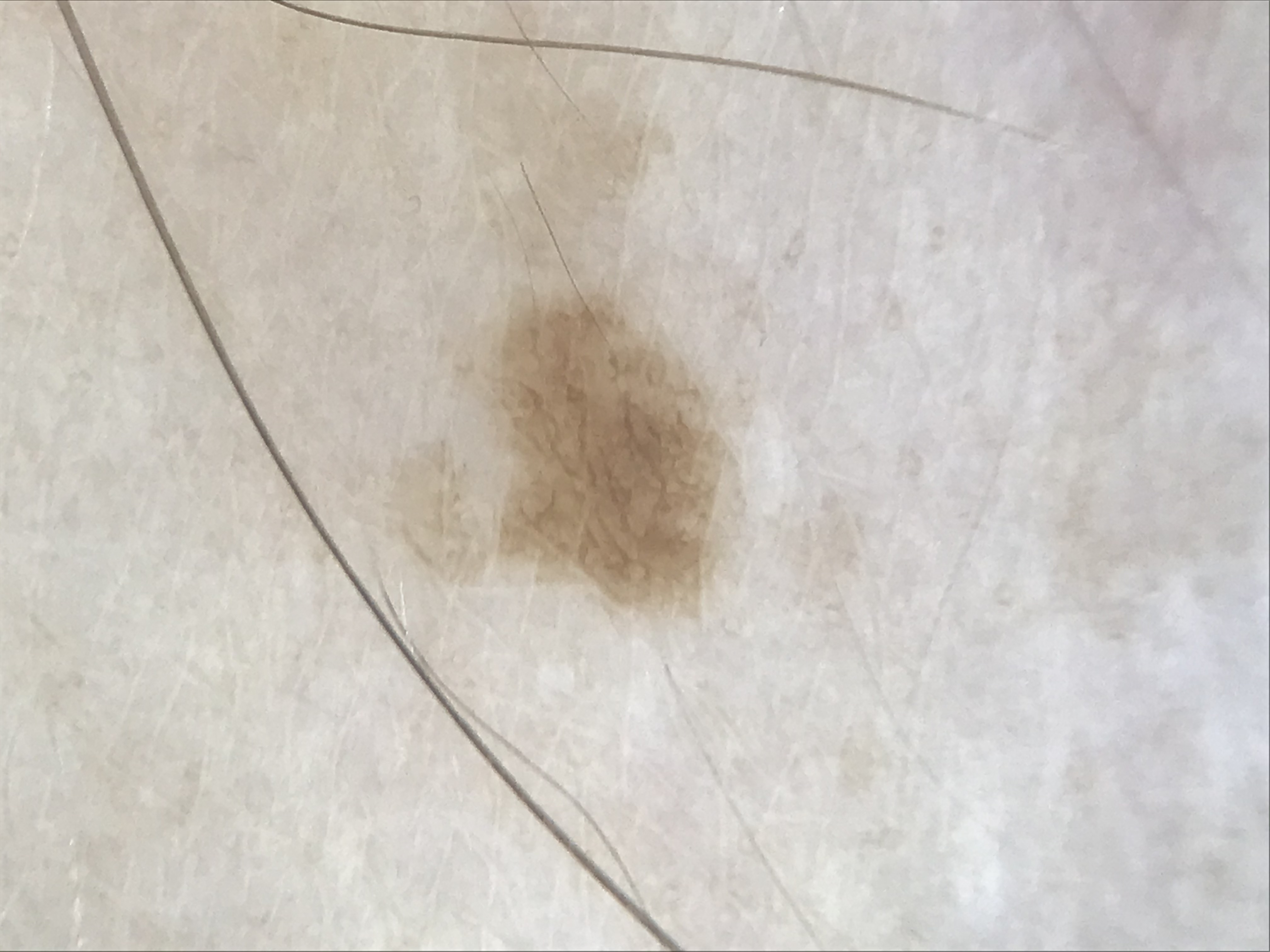A dermoscopic photograph of a skin lesion.
This is a banal lesion.
Consistent with a junctional nevus.